The photograph was taken at an angle: 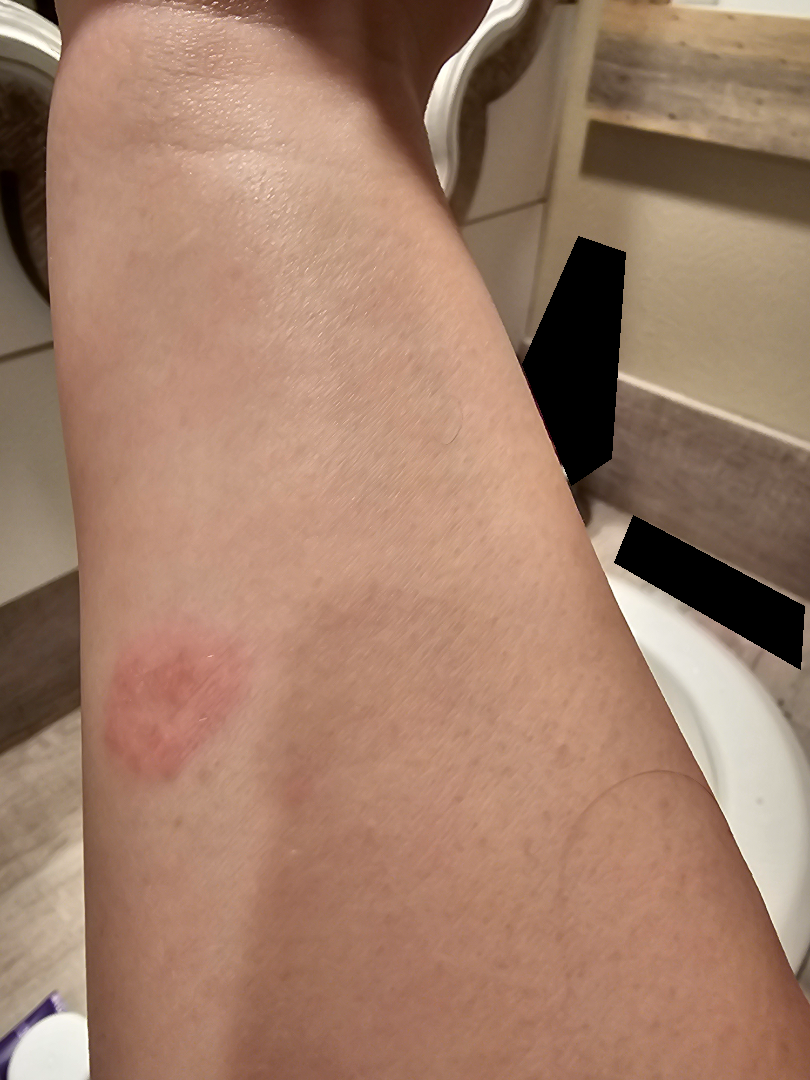On photographic review, most consistent with Basal Cell Carcinoma; possibly SCC/SCCIS; a remote consideration is Infected eczema.